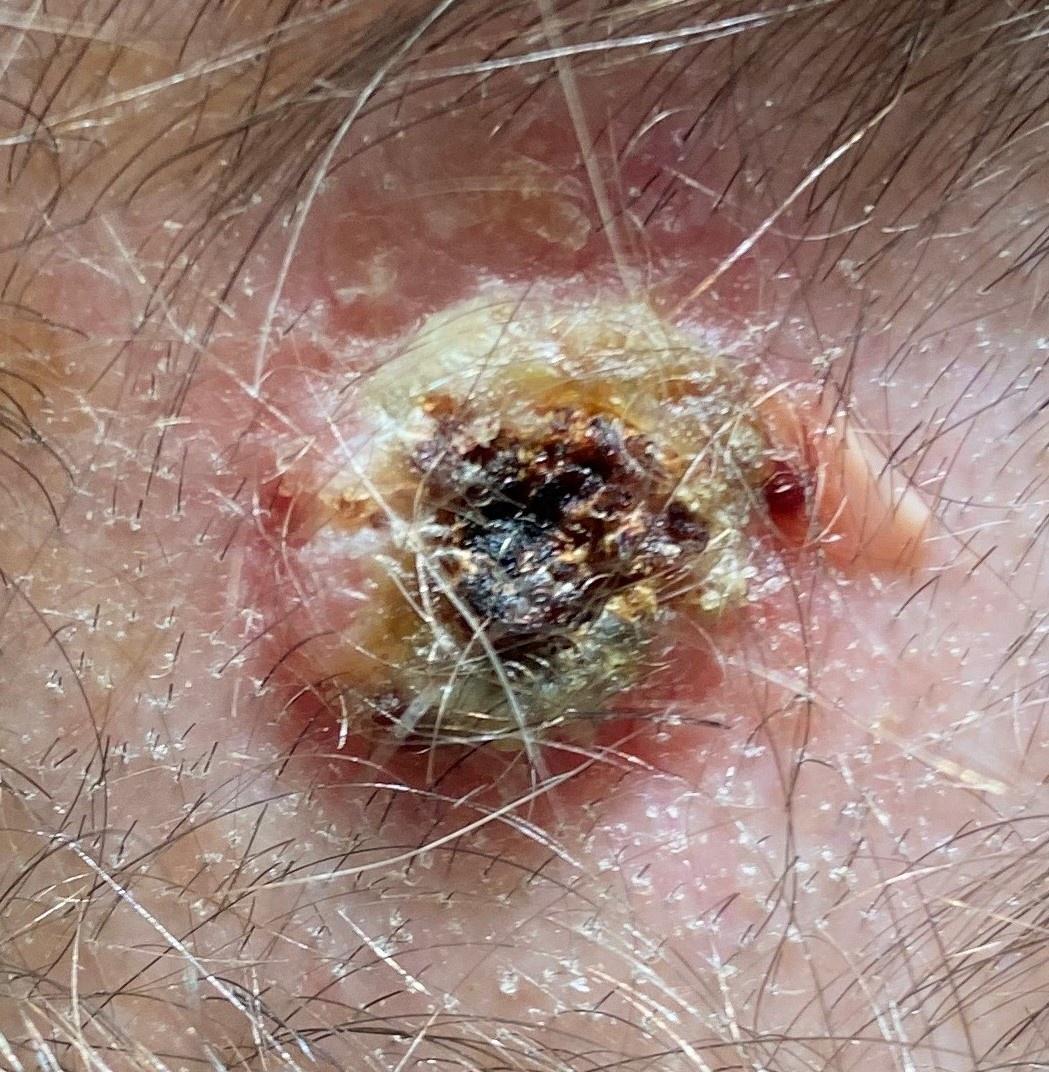Q: Skin phototype?
A: II
Q: What is the anatomic site?
A: the head or neck
Q: What is the diagnosis?
A: Basal cell carcinoma (biopsy-proven)